A subject 52 years old; a clinical close-up photograph of a skin lesion: 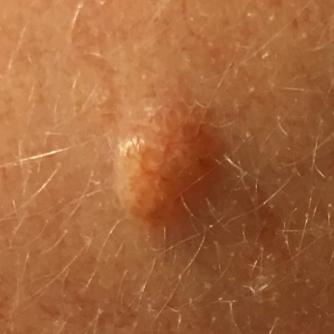Summary:
The lesion is on the face. Per patient report, the lesion is elevated, but does not itch and has not grown.
Impression:
The consensus clinical diagnosis was a nevus.